The affected area is the leg. The photo was captured at a distance. Symptoms reported: burning and pain. The lesion is described as raised or bumpy. The condition has been present for about one day. Fitzpatrick skin type II.
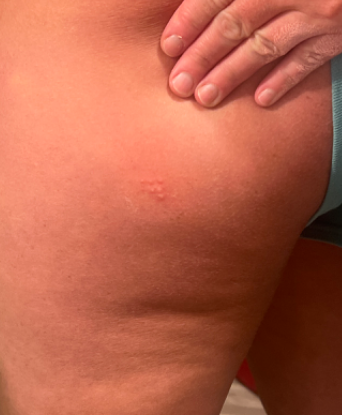Q: What is the dermatologist's impression?
A: the differential is split between Acne, Molluscum Contagiosum and Herpes Simplex